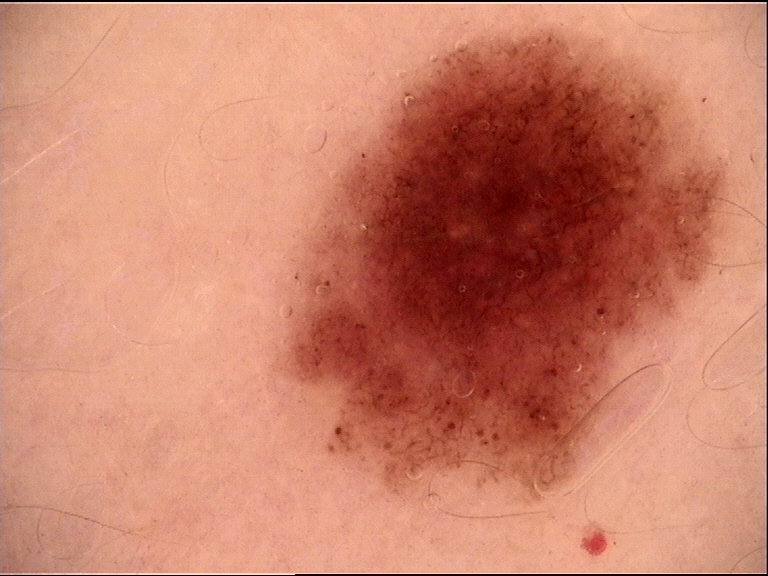| field | value |
|---|---|
| diagnosis | dysplastic compound nevus (expert consensus) |